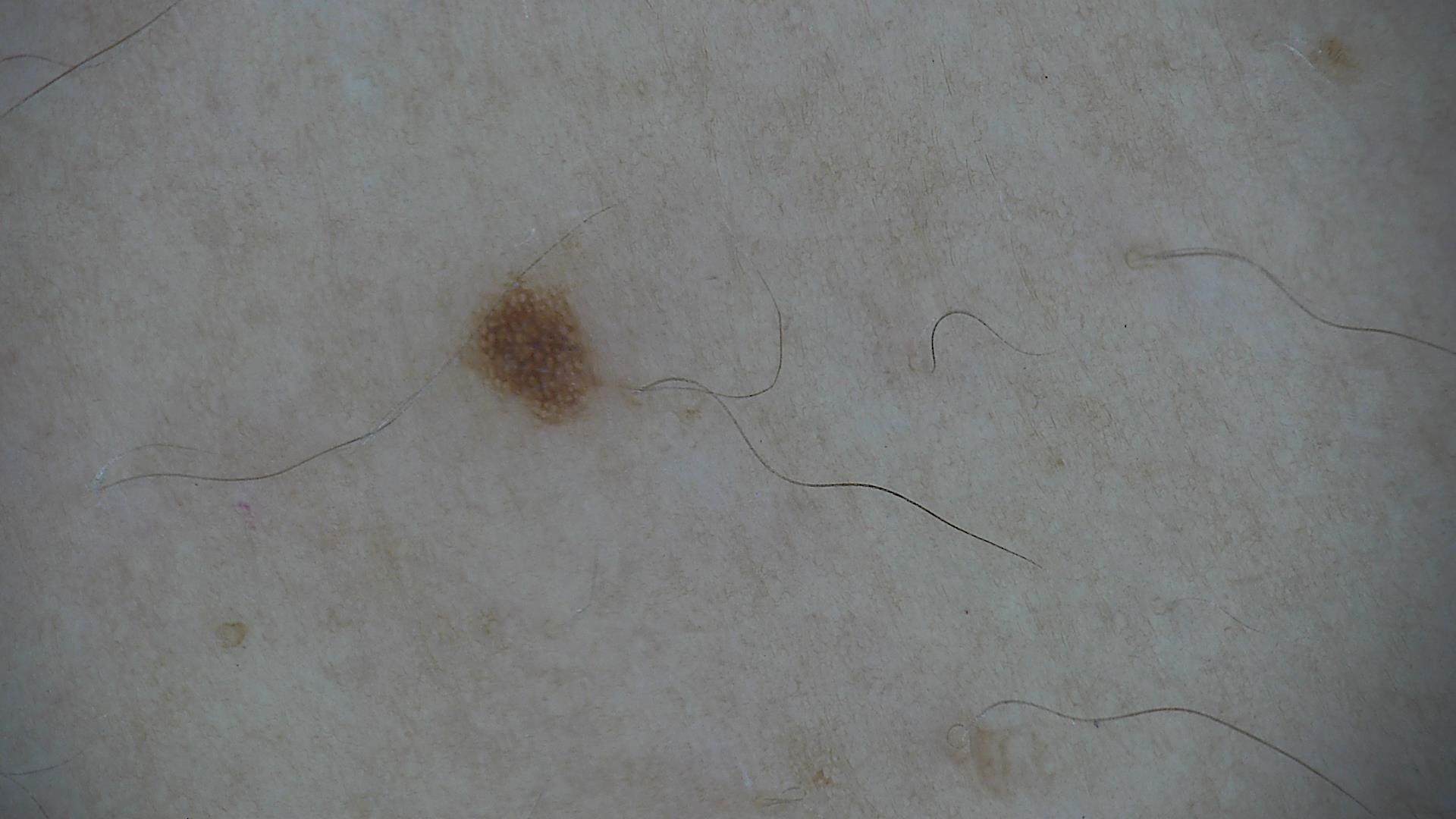A dermoscopy image of a single skin lesion. Consistent with a benign lesion — a dysplastic junctional nevus.